A subject 61 years old:
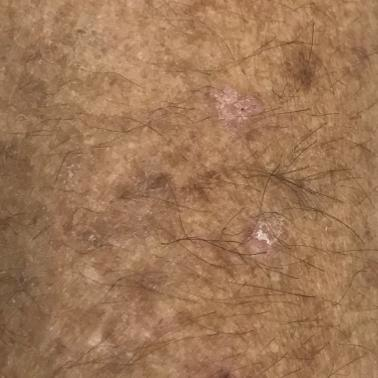Findings: The patient describes that the lesion itches, but has not bled. Impression: Clinically diagnosed as a lesion of indeterminate malignant potential — an actinic keratosis.